An image taken at an angle: 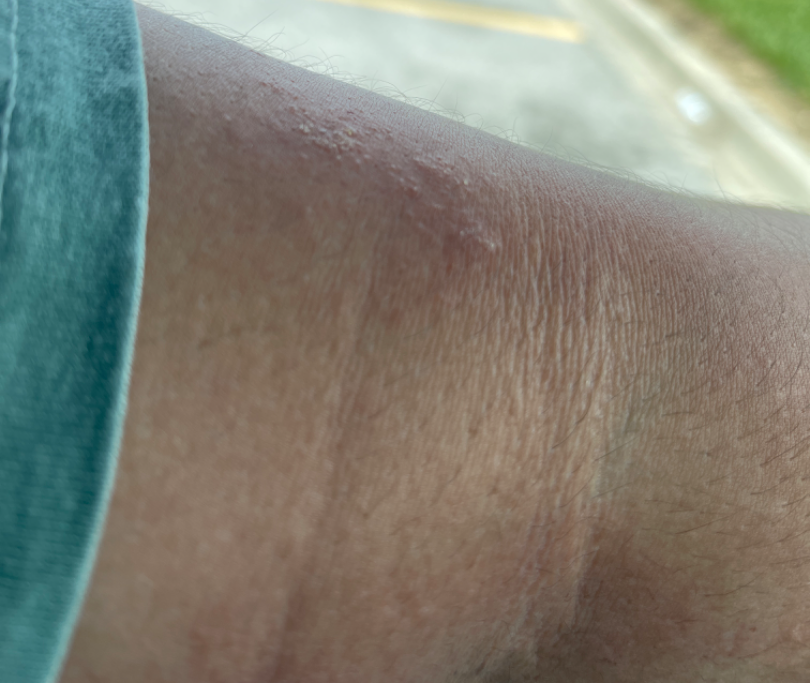Case summary:
- impression: Acute and chronic dermatitis (leading)